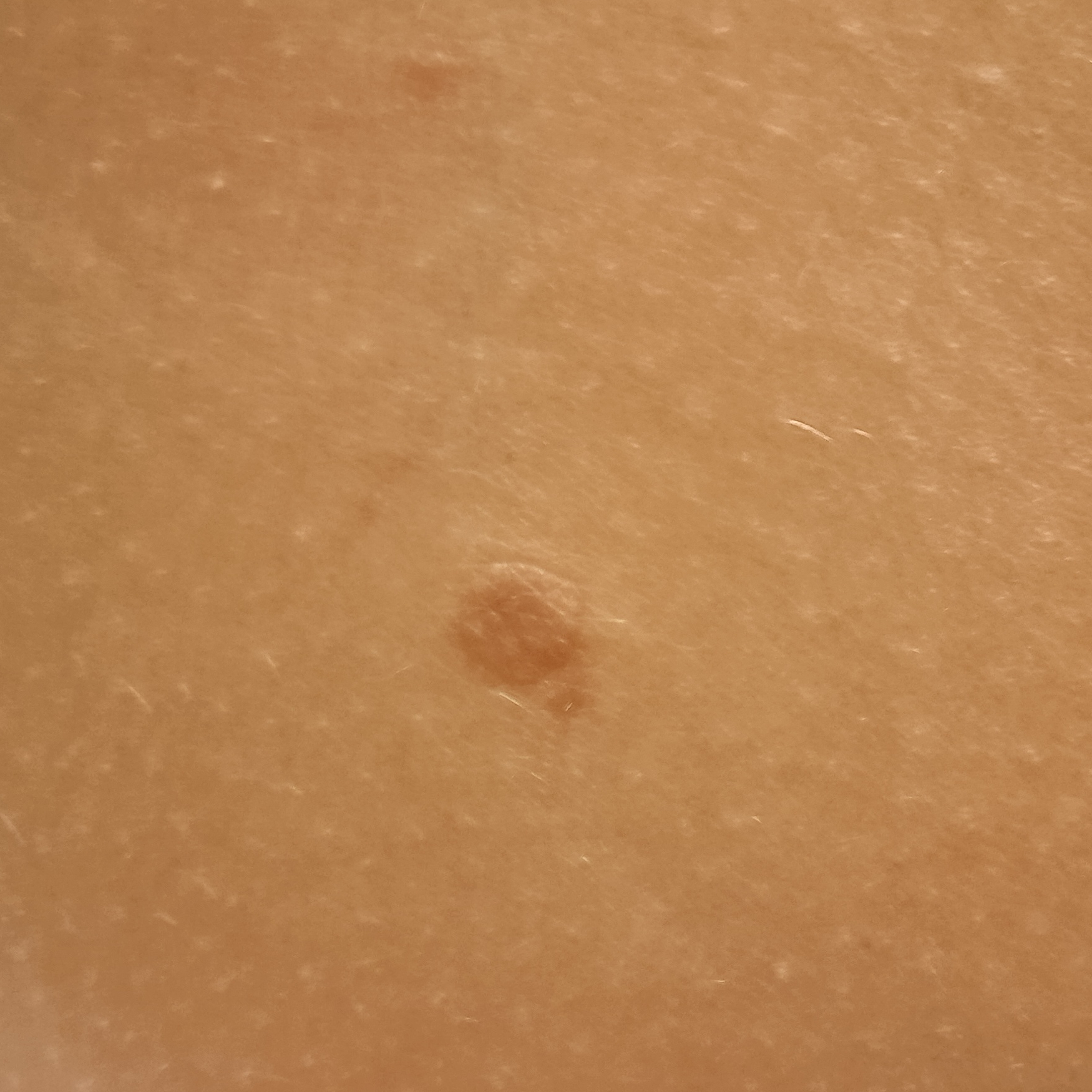A confident diagnosis could not be established from review. sun reaction: skin tans without first burning | patient: female, 47 years of age | modality: clinical photo | relevant history: a history of sunbed use | referral: research study (no referral diagnosis) | nevus count: a moderate number of melanocytic nevi | body site: an arm | lesion size: 8.1 mm.